Close-up view: 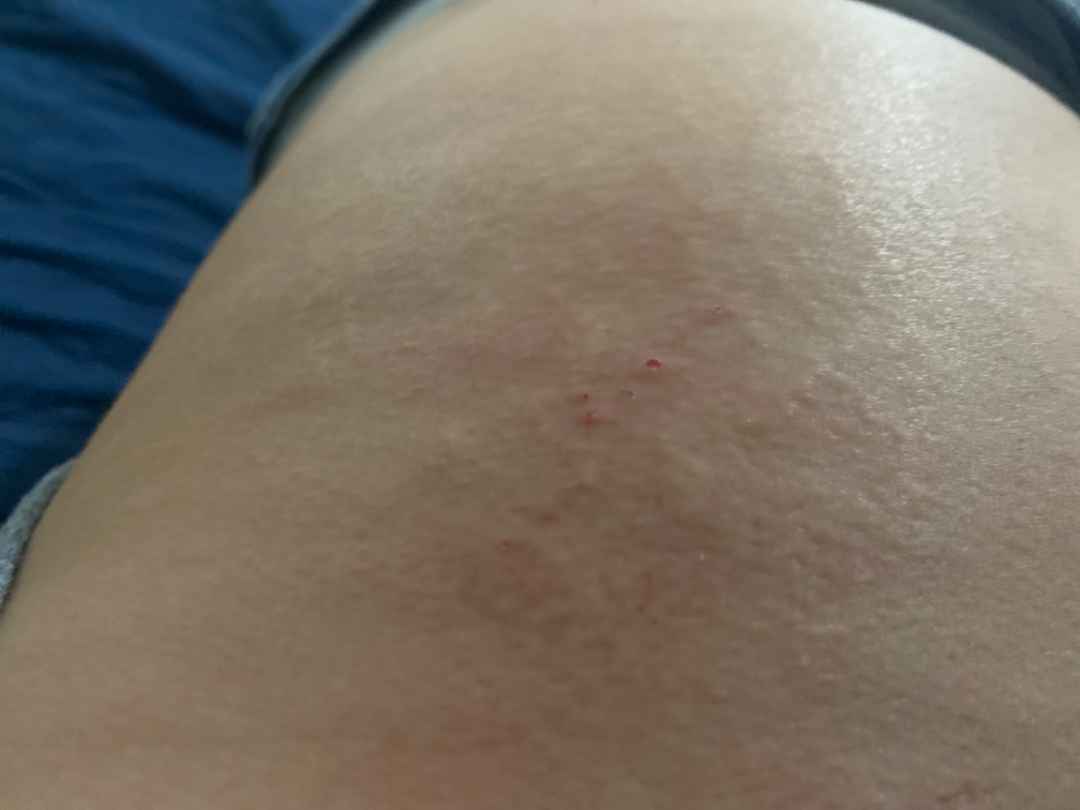Notes:
• self-categorized as: a rash
• texture: raised or bumpy
• dermatologist impression: Eczema (55%); Contact dermatitis, NOS (27%); Urticaria (18%)